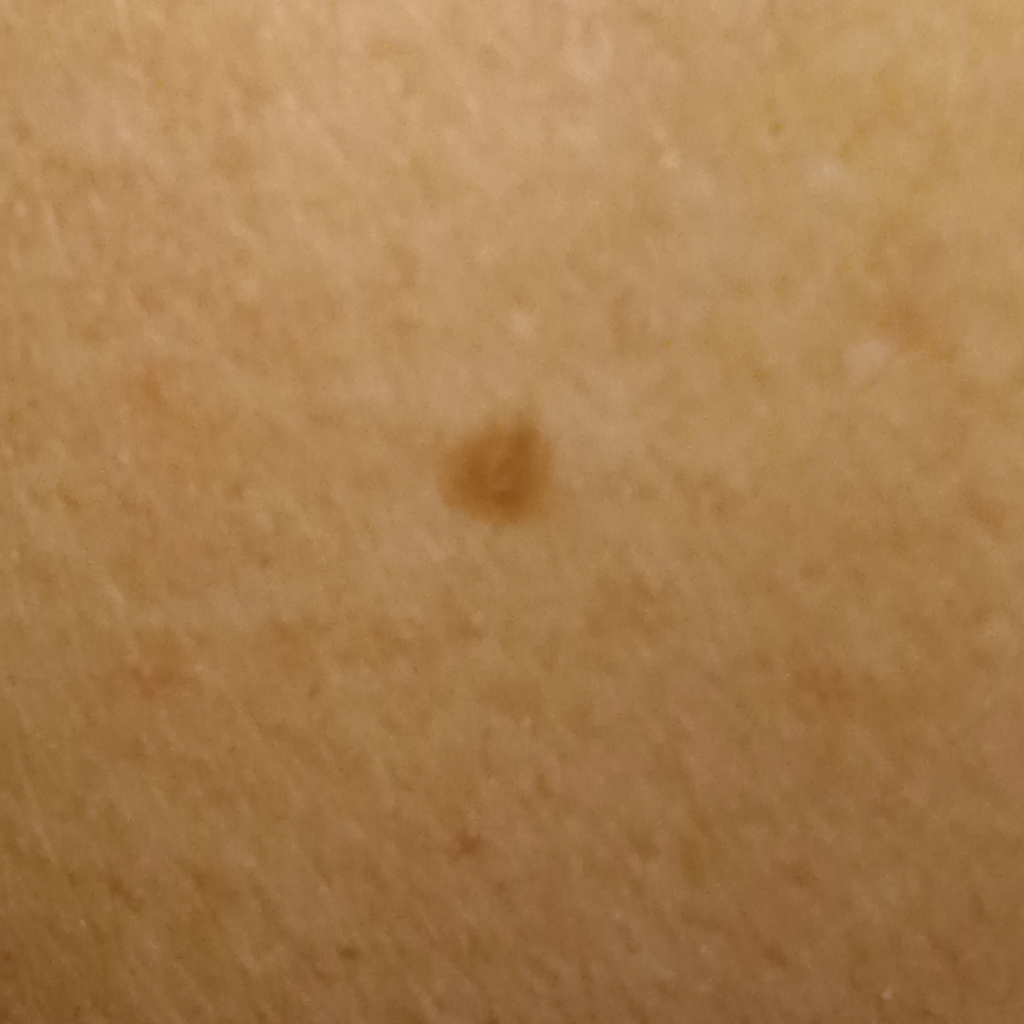Case:
* sun reaction — skin tans without first burning
* subject — female, age 60
* image type — clinical photo
* referral context — research study (no referral diagnosis)
* risk factors — a personal history of skin cancer, a personal history of cancer
* nevus count — few melanocytic nevi overall
* site — an arm
* size — 2.8 mm
* diagnostic label — melanocytic nevus (dermatologist consensus)